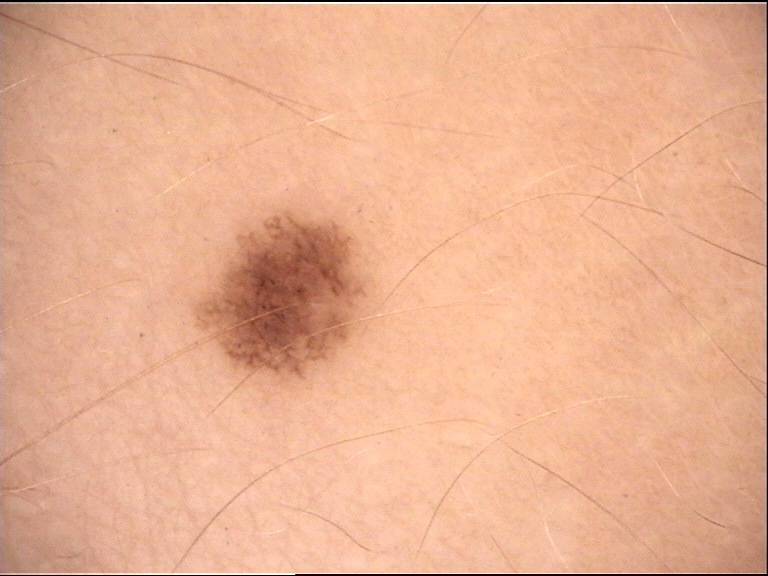The diagnostic label was a junctional nevus.